This is a close-up image; located on the head or neck and front of the torso:
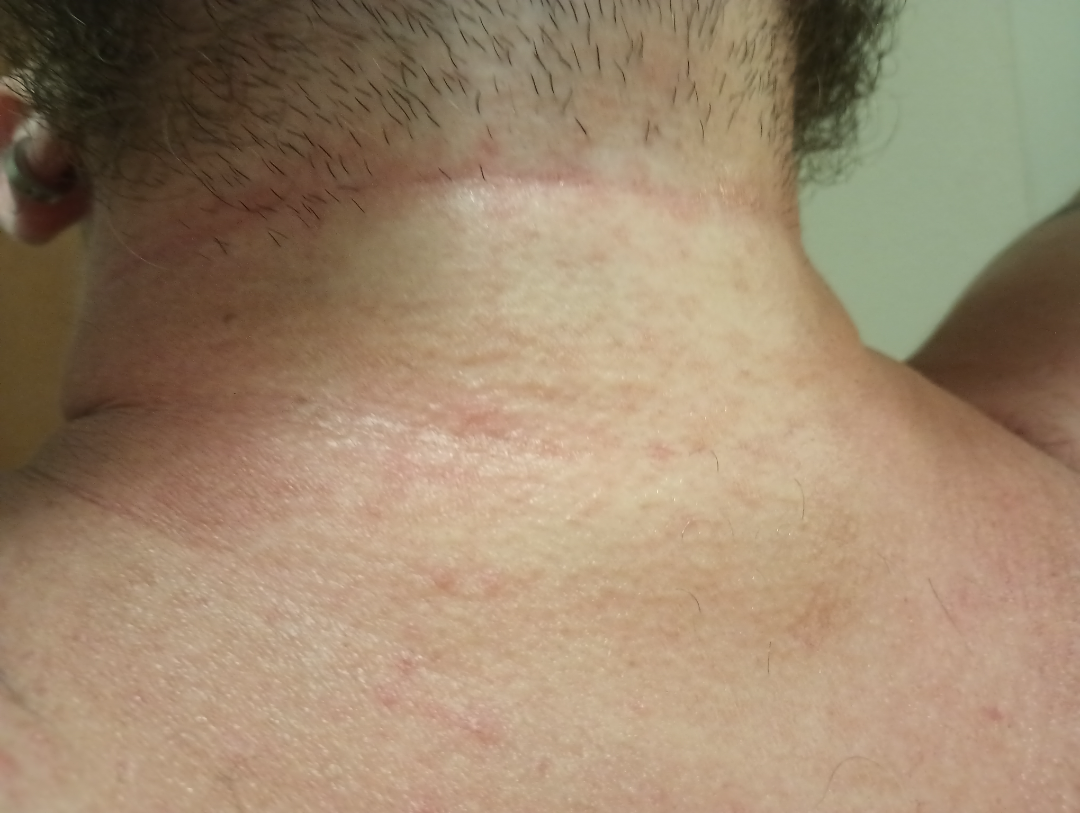assessment = could not be assessed.